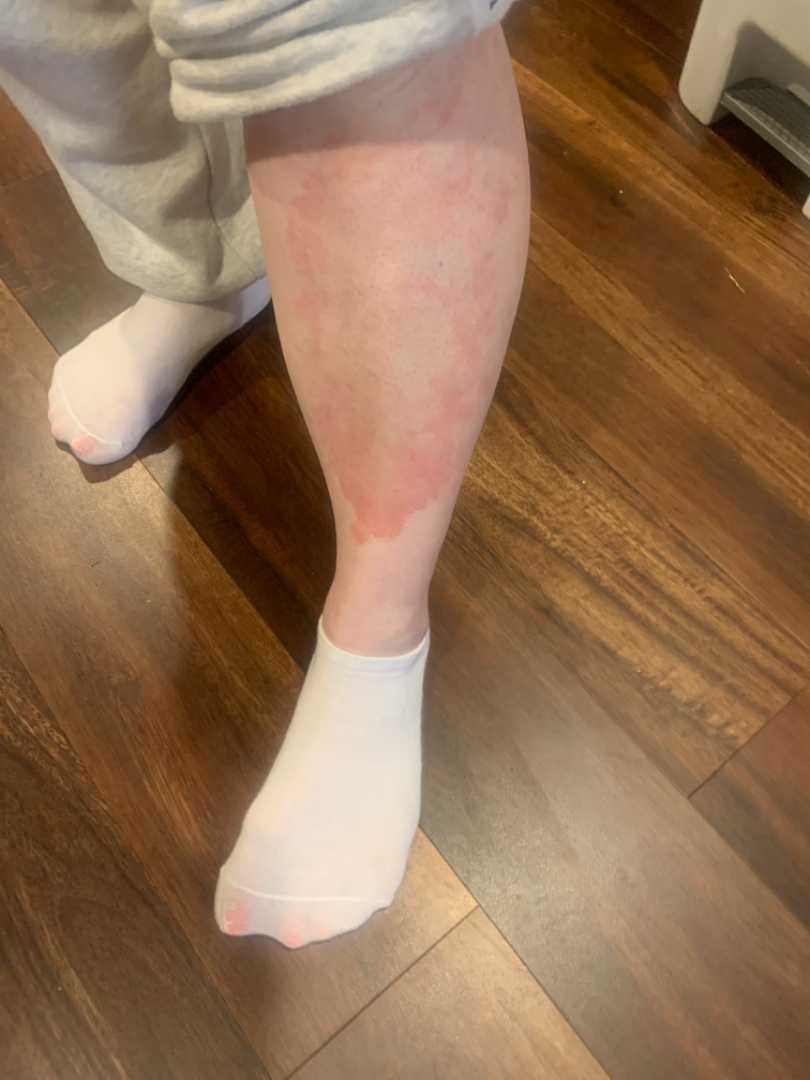Findings: The reviewing clinician's impression was: the differential is split between Psoriasis, Acute and chronic dermatitis and Necrobiosis lipoidica.